A dermatoscopic image of a skin lesion: 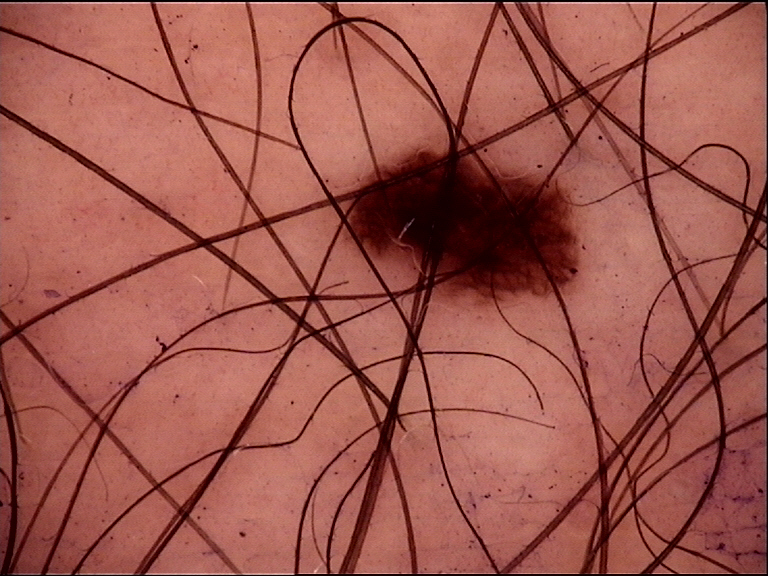{"lesion_type": {"main_class": "banal", "pattern": "junctional"}, "diagnosis": {"name": "junctional nevus", "code": "jb", "malignancy": "benign", "super_class": "melanocytic", "confirmation": "expert consensus"}}